A dermoscopic image of a skin lesion; a male subject in their mid- to late 80s or older — 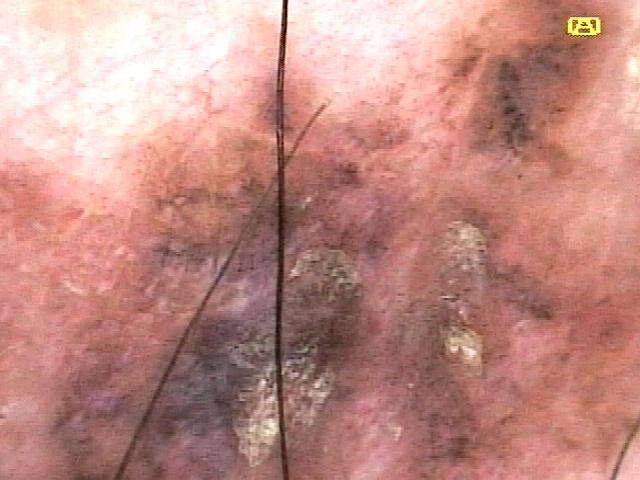The lesion was found on a lower extremity. Histopathology confirmed a melanoma.